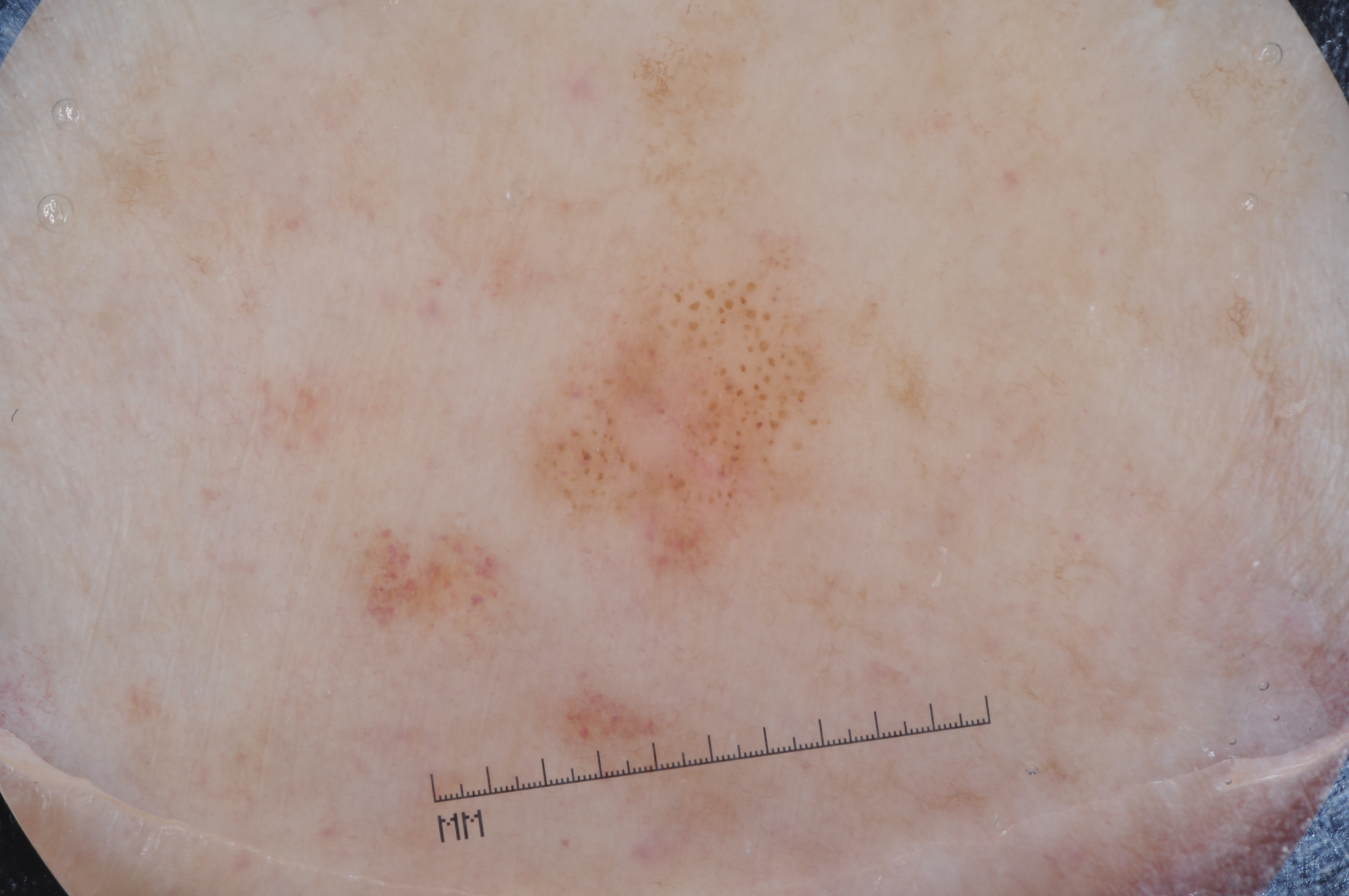image:
  modality: dermoscopy
patient:
  sex: female
  age_approx: 85+
lesion_extent: moderate
lesion_location:
  bbox_xyxy:
    - 505
    - 201
    - 859
    - 623
dermoscopic_features:
  present: []
  absent:
    - streaks
    - negative network
    - pigment network
    - milia-like cysts
diagnosis:
  name: melanoma
  malignancy: malignant
  lineage: melanocytic
  provenance: histopathology